This image was taken at an angle: 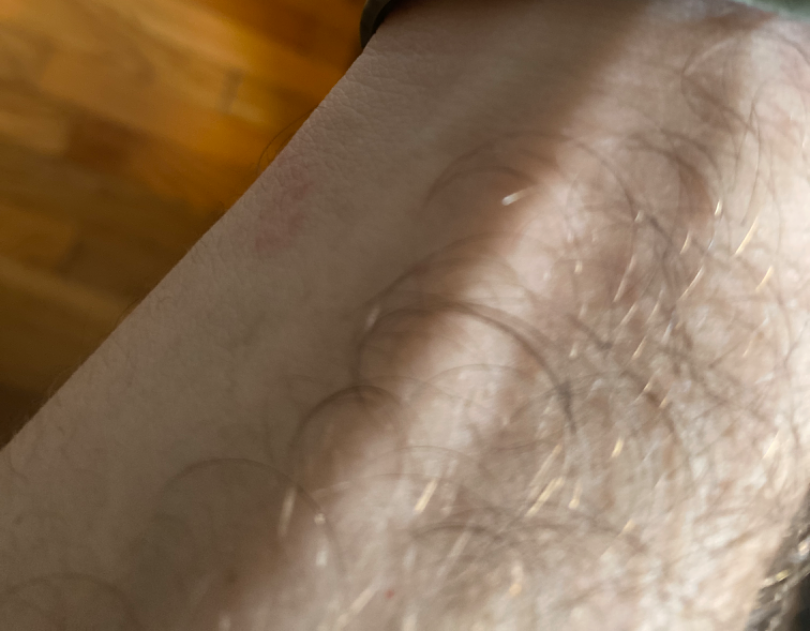impression = reviewed remotely by one dermatologist: the differential, in no particular order, includes Eczema, Allergic Contact Dermatitis and Irritant Contact Dermatitis